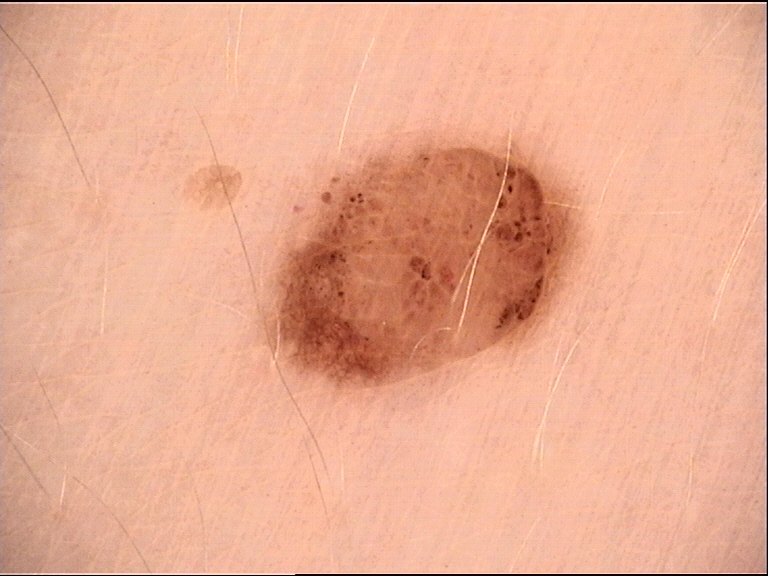modality=dermatoscopy
classification=banal
assessment=dermal nevus (expert consensus)